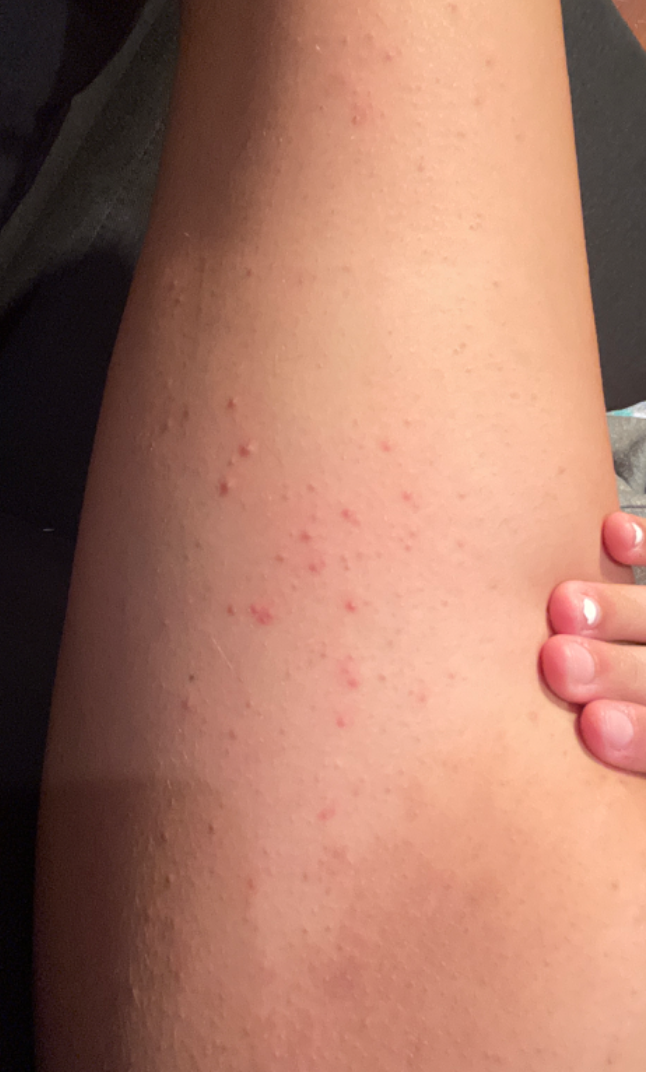Notes:
* diagnostic considerations: the primary impression is Folliculitis; also raised was Keratosis pilaris; lower on the differential is Eczema